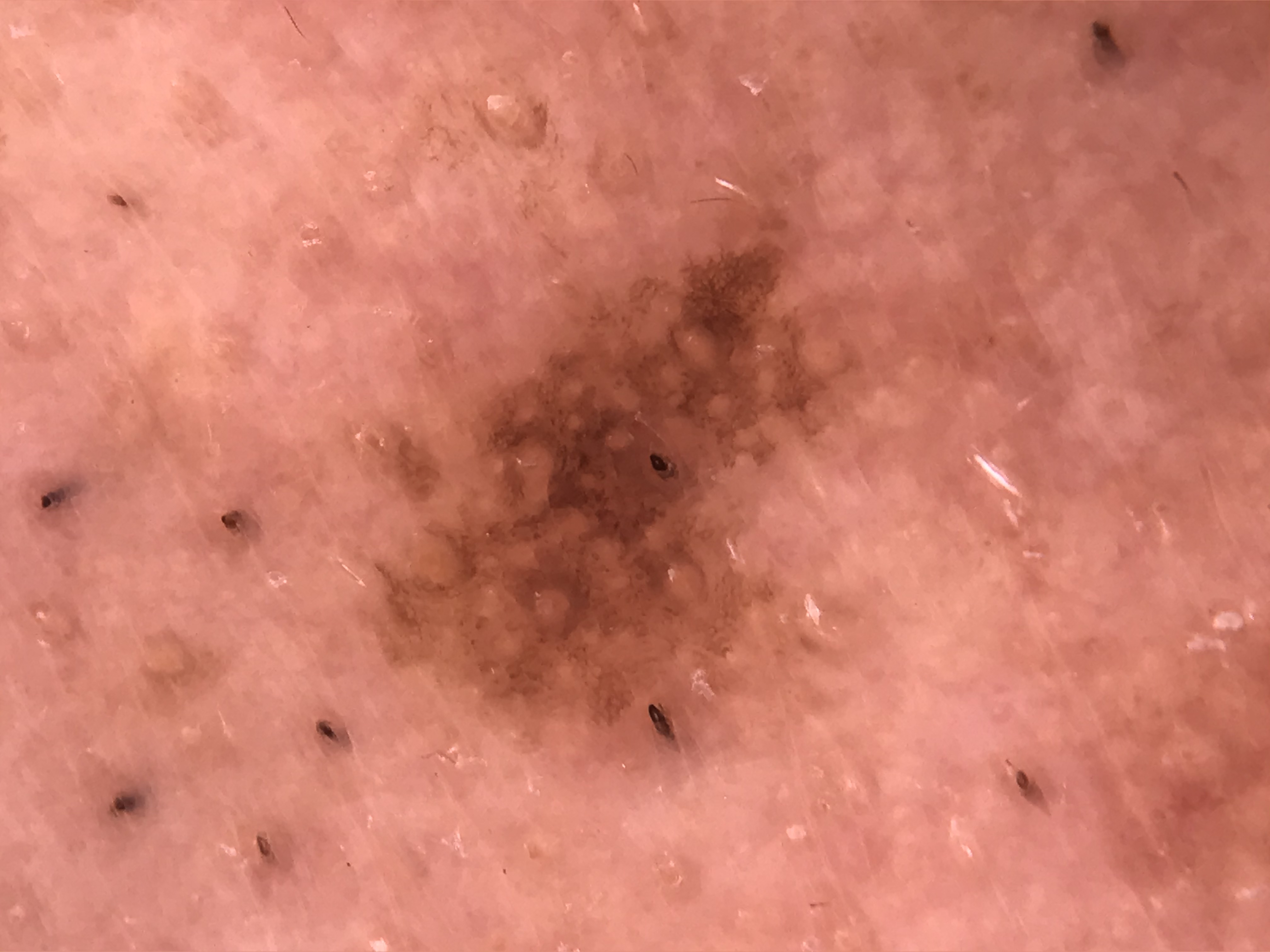Dermoscopy of a skin lesion. The architecture is that of a keratinocytic lesion. Consistent with a benign lesion — a seborrheic keratosis.